A close-up photograph; the affected area is the top or side of the foot — 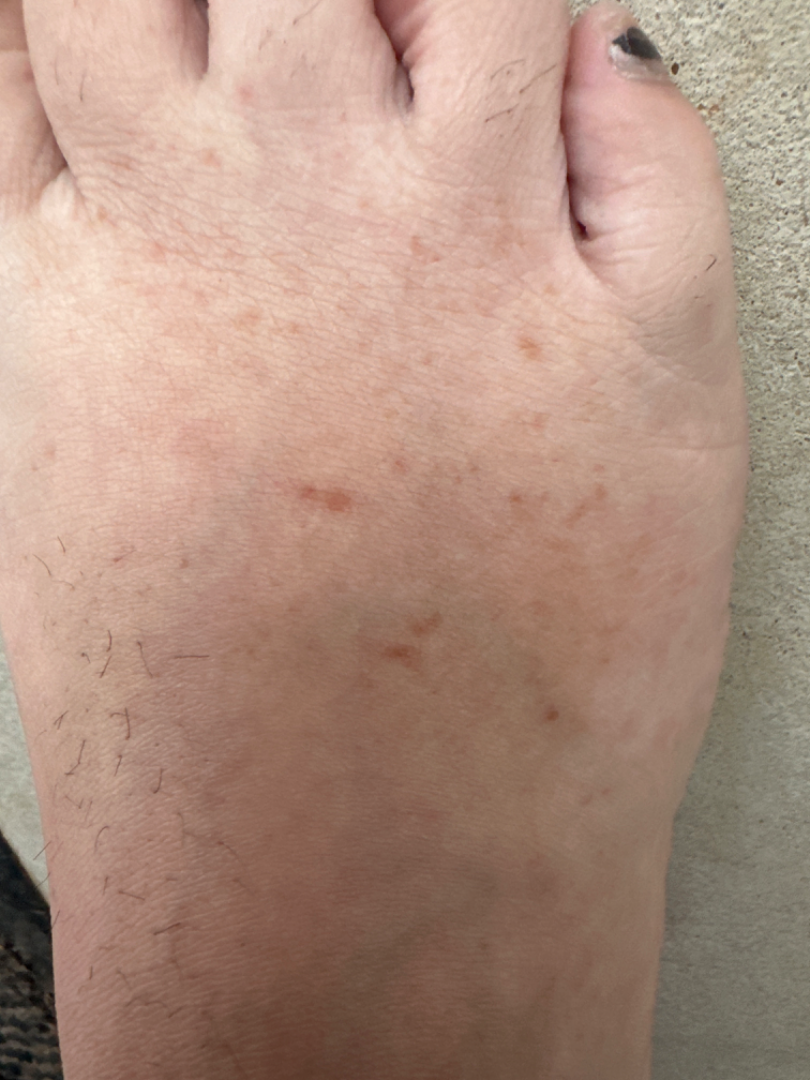The case was indeterminate on photographic review. Present for one to three months. No relevant systemic symptoms. Texture is reported as flat.